A clinical photograph showing a skin lesion. A patient 86 years of age.
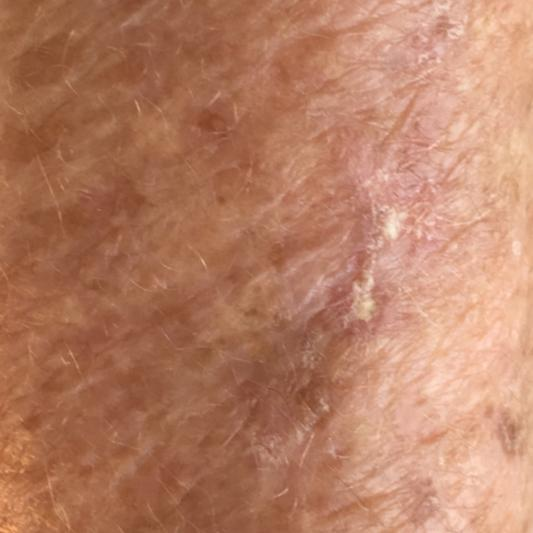Located on an arm.
By the patient's account, the lesion itches.
Diagnosed by dermatologist consensus as a lesion of indeterminate malignant potential — an actinic keratosis.